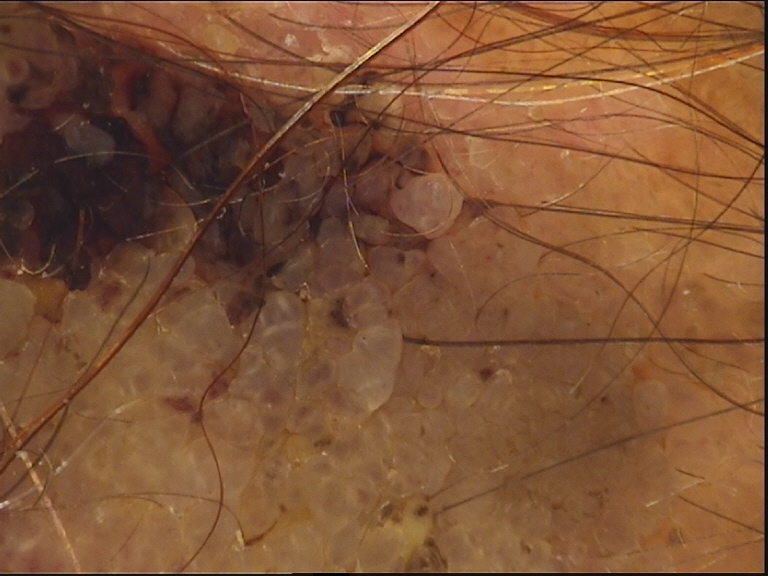Labeled as a dermal nevus.